A dermoscopy image of a single skin lesion:
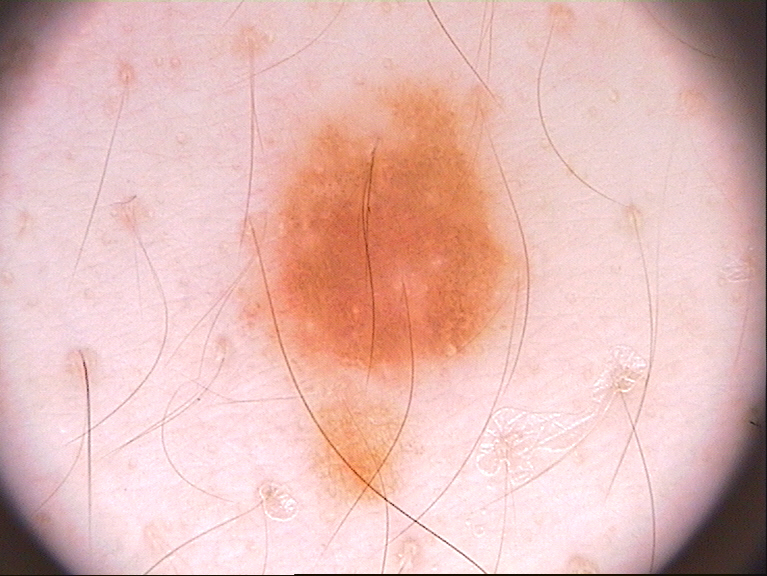lesion bbox = [236, 72, 532, 395]
dermoscopic findings = negative network and pigment network; absent: globules, milia-like cysts, and streaks
size = moderate
impression = a melanocytic nevus